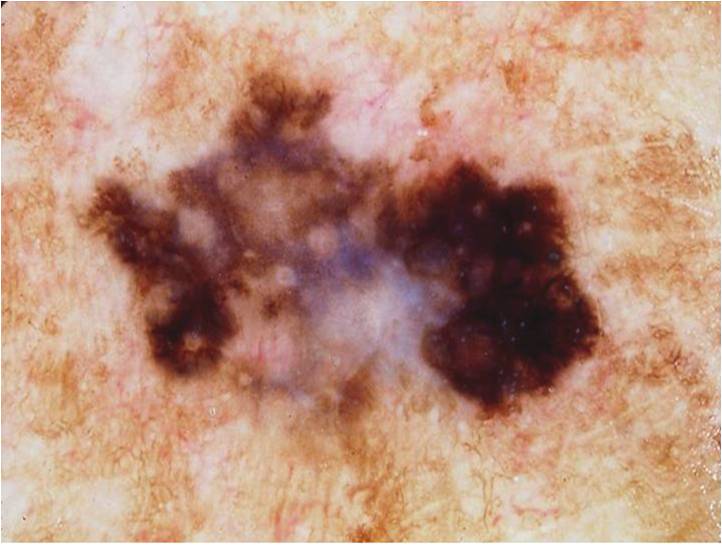Case summary:
– image · dermoscopy of a skin lesion
– lesion extent · large
– lesion location · x1=65 y1=65 x2=611 y2=424
– diagnostic label · a malignancy